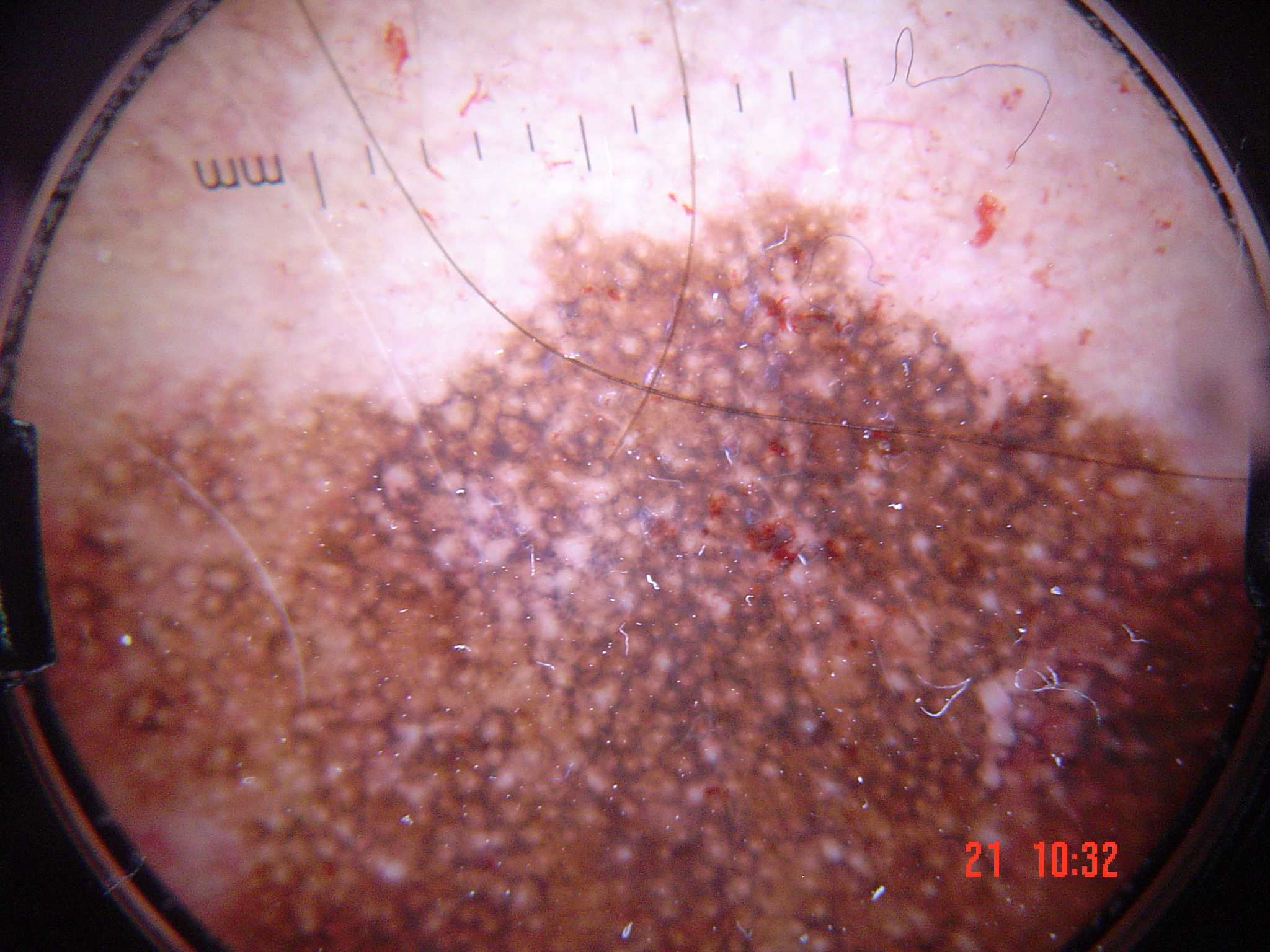image: dermoscopy
diagnosis:
  name: lentigo maligna
  code: lm
  malignancy: malignant
  super_class: melanocytic
  confirmation: histopathology